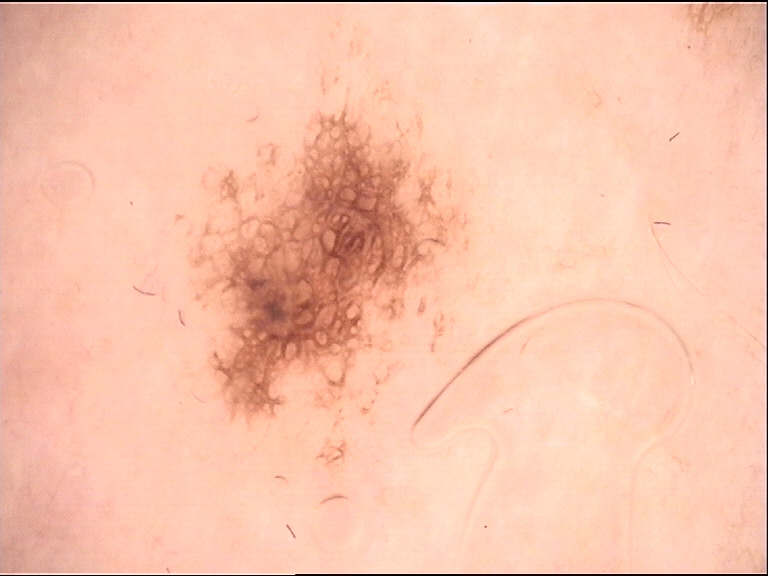Impression:
The diagnosis was a dysplastic junctional nevus.